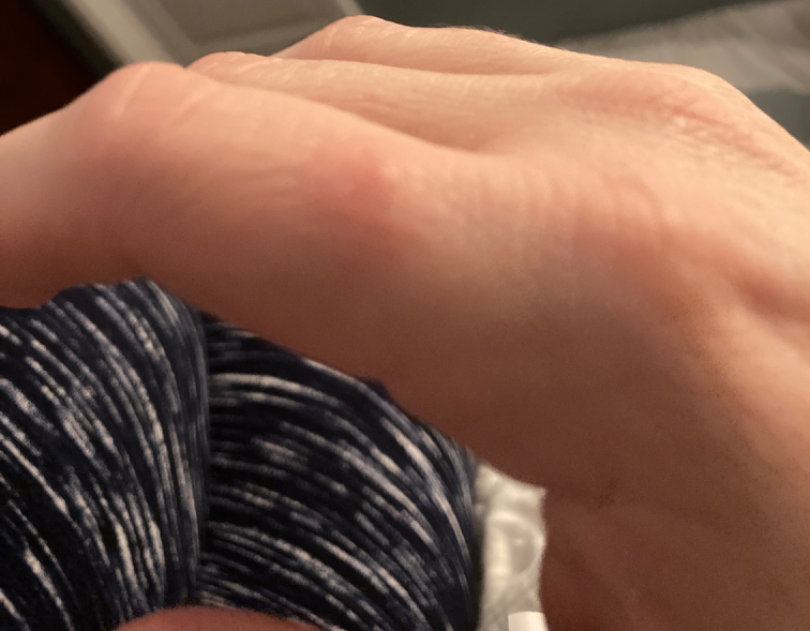* clinical impression — most likely Pyogenic granuloma